A dermoscopic close-up of a skin lesion: 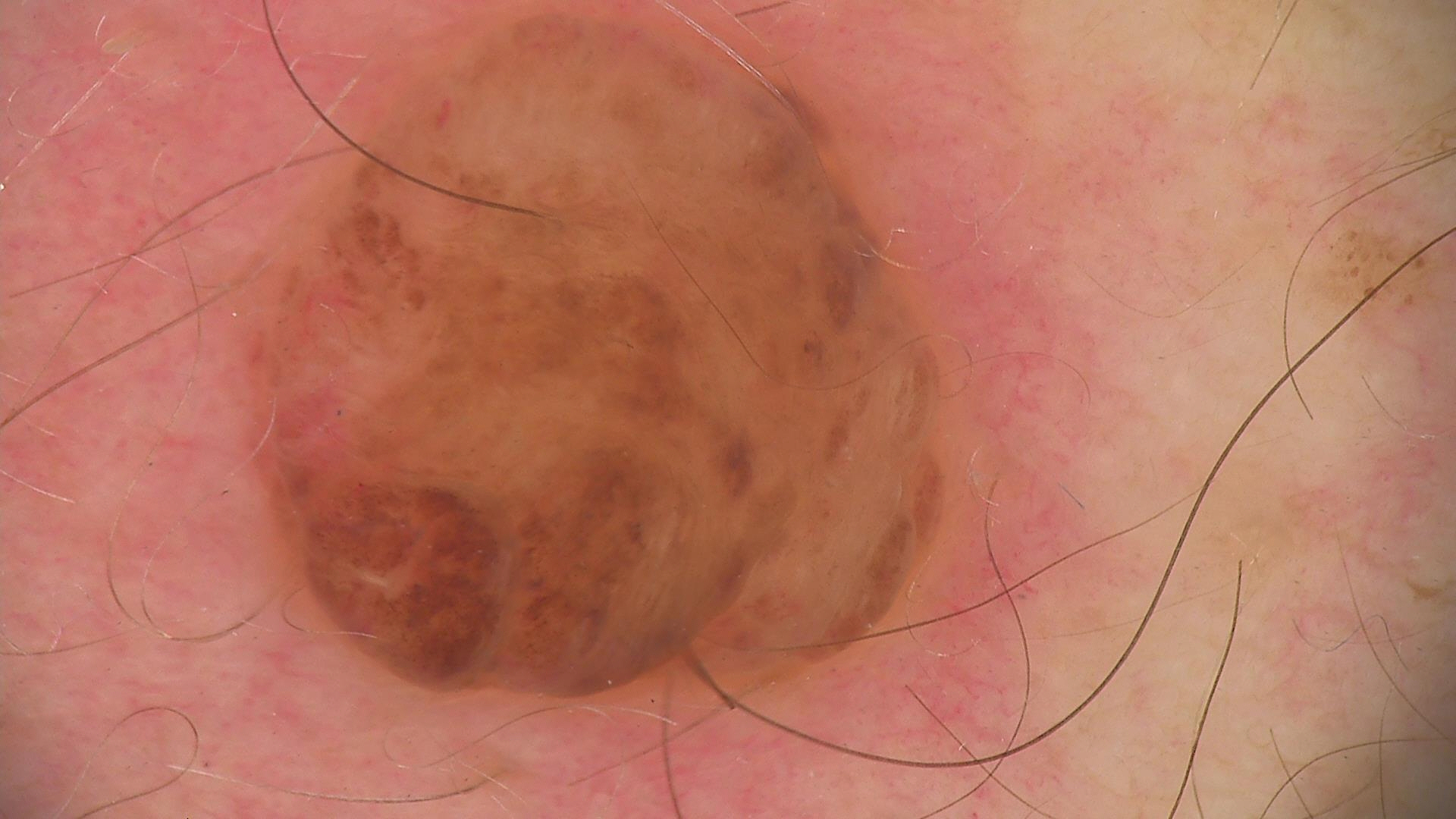Classified as a banal lesion — a dermal nevus.